Reported duration is about one day; the patient considered this a rash; the patient notes associated chills and fatigue; the back of the hand, arm and top or side of the foot are involved; this is a close-up image; the lesion is described as fluid-filled, rough or flaky and raised or bumpy; reported lesion symptoms include burning, itching, bothersome appearance, enlargement and pain; skin tone: Fitzpatrick phototype II.
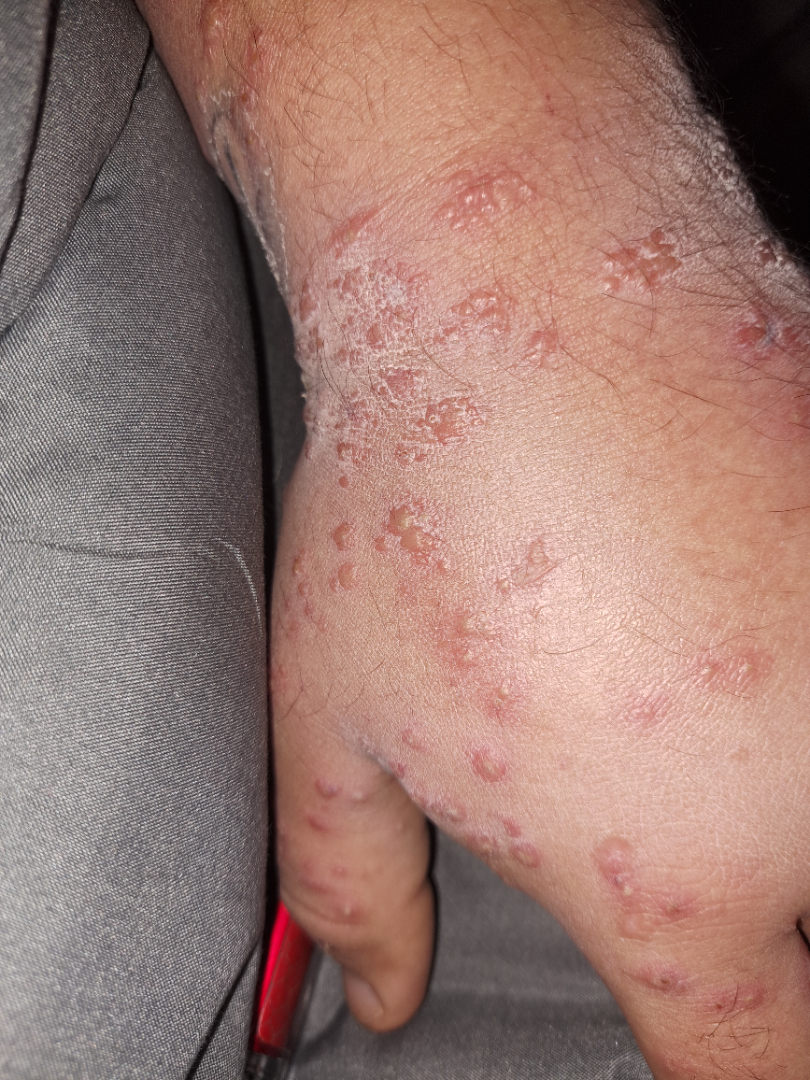differential diagnosis: Contact dermatitis (leading); Allergic Contact Dermatitis (possible); Insect Bite (possible); Acute generalised exanthematous pustulosis (possible)